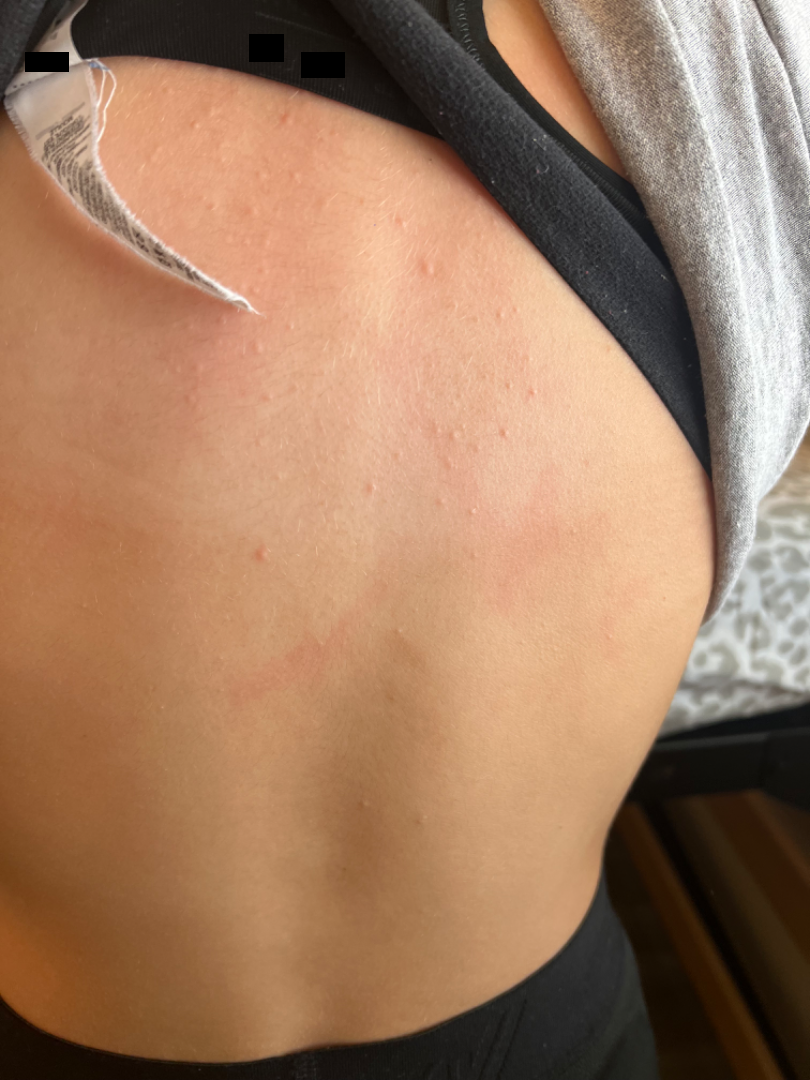The photograph is a close-up of the affected area. The lesion is described as raised or bumpy. The condition has been present for about one day. The back of the torso is involved. Reported lesion symptoms include itching. Most likely Folliculitis; the differential also includes Acne.